A dermoscopy image of a single skin lesion.
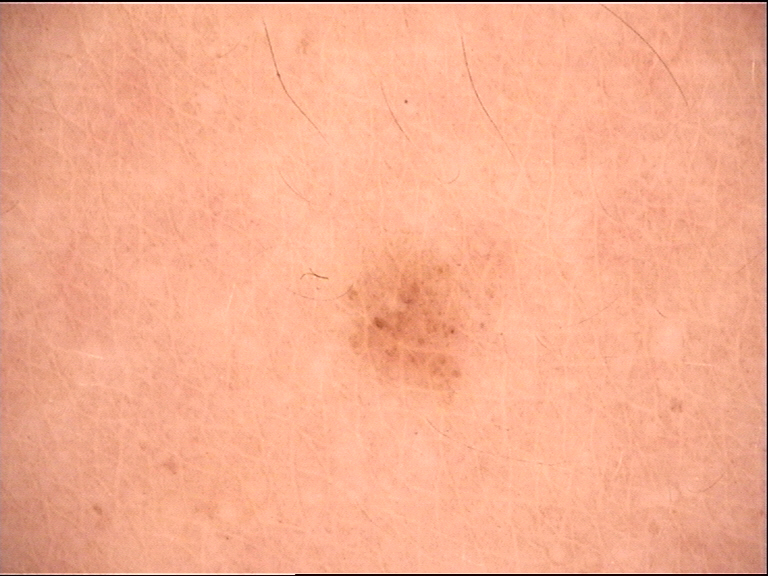{
  "diagnosis": {
    "name": "dysplastic junctional nevus",
    "code": "jd",
    "malignancy": "benign",
    "super_class": "melanocytic",
    "confirmation": "expert consensus"
  }
}